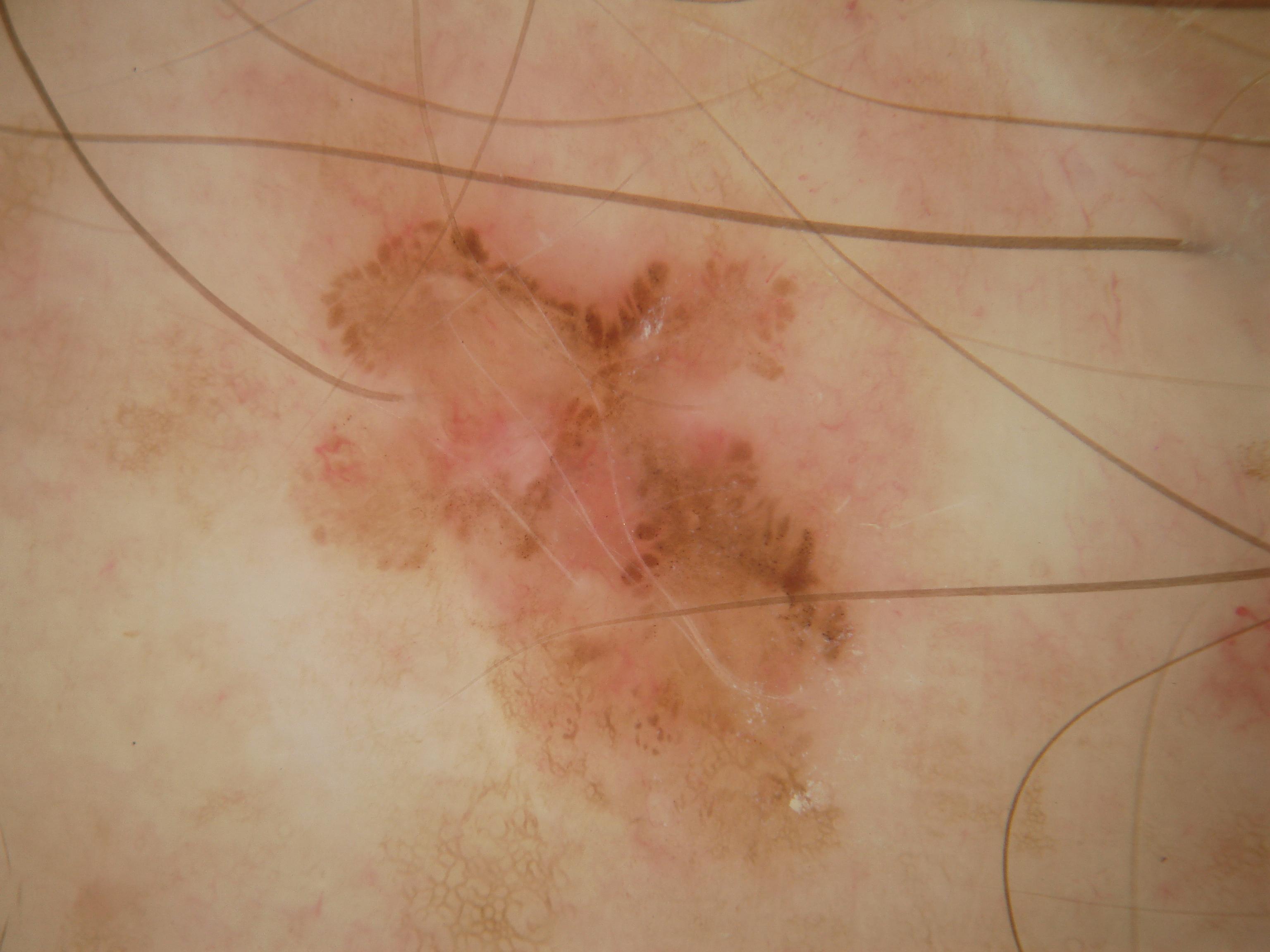patient = male, approximately 65 years of age | image = dermoscopic image | lesion size = moderate | dermoscopic findings = streaks and globules; absent: negative network, pigment network, and milia-like cysts | lesion bbox = bbox=[305, 214, 862, 875] | diagnosis = a melanoma, a skin cancer.